Female contributor, age 60–69 · the photograph was taken at a distance · located on the back of the hand, palm and arm.
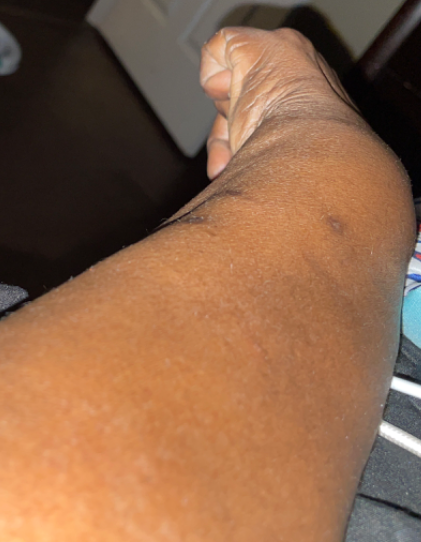The reviewing dermatologist was unable to assign a differential diagnosis from the image. The contributor reports the lesion is rough or flaky. Skin tone: Fitzpatrick skin type V; lay reviewers estimated Monk Skin Tone 5 or 7 (two reviewer pools disagreed). Symptoms reported: bothersome appearance. Reported duration is three to twelve months. The patient considered this acne. The patient also reports fatigue.